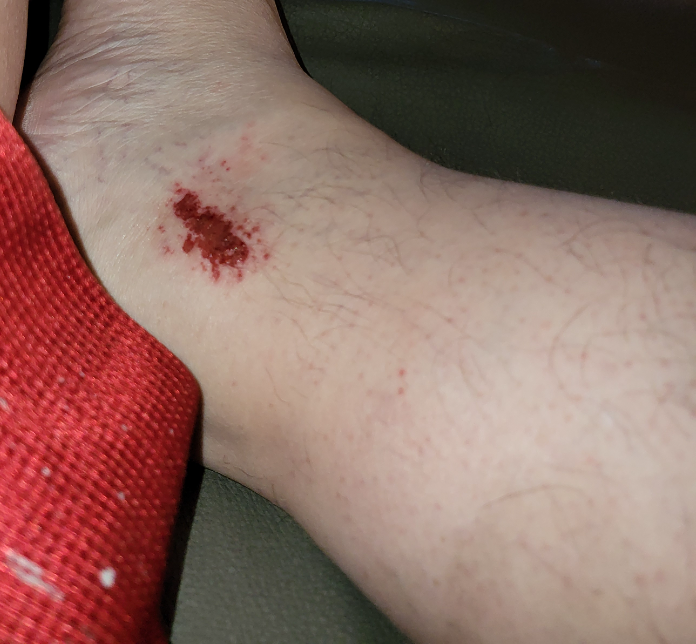Findings:
– location: top or side of the foot
– view: at a distance
– differential diagnosis: the leading consideration is Superficial wound of body region; also consider superficial hemorrhage; possibly Blister